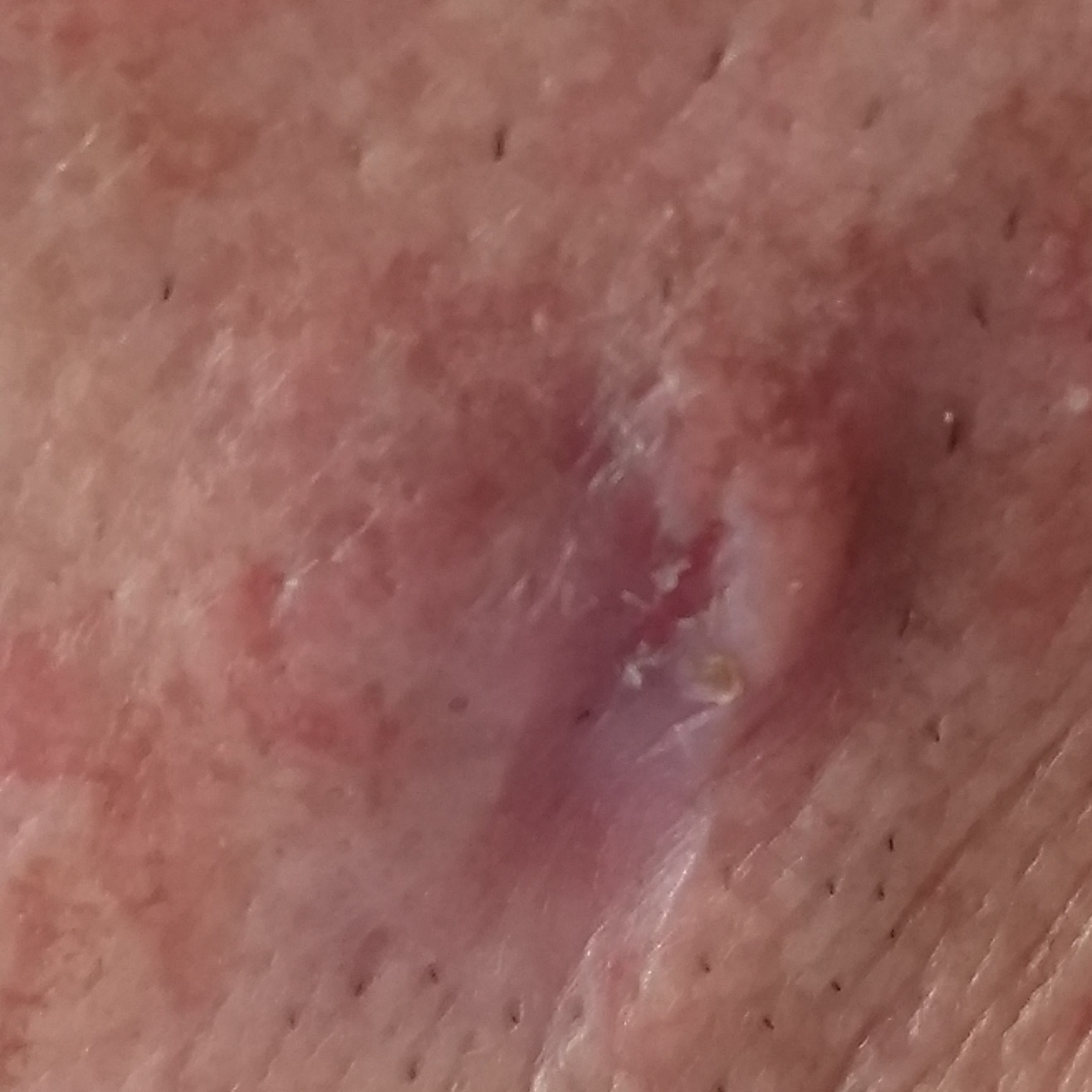Summary: A clinical photograph of a skin lesion. Recorded as Fitzpatrick skin type II. A male patient 43 years of age. The chart records pesticide exposure. The lesion is located on the face. The lesion measures 15 × 13 mm. By the patient's account, the lesion is elevated, itches, has grown, and has bled. Conclusion: Confirmed on histopathology as a malignancy — a basal cell carcinoma.